The contributor reports the lesion is raised or bumpy · the condition has been present for about one day · no relevant systemic symptoms · the patient considered this a rash · a close-up photograph · the subject is female · reported lesion symptoms include enlargement, pain, burning, bothersome appearance and itching · the lesion involves the leg, arm and back of the hand — 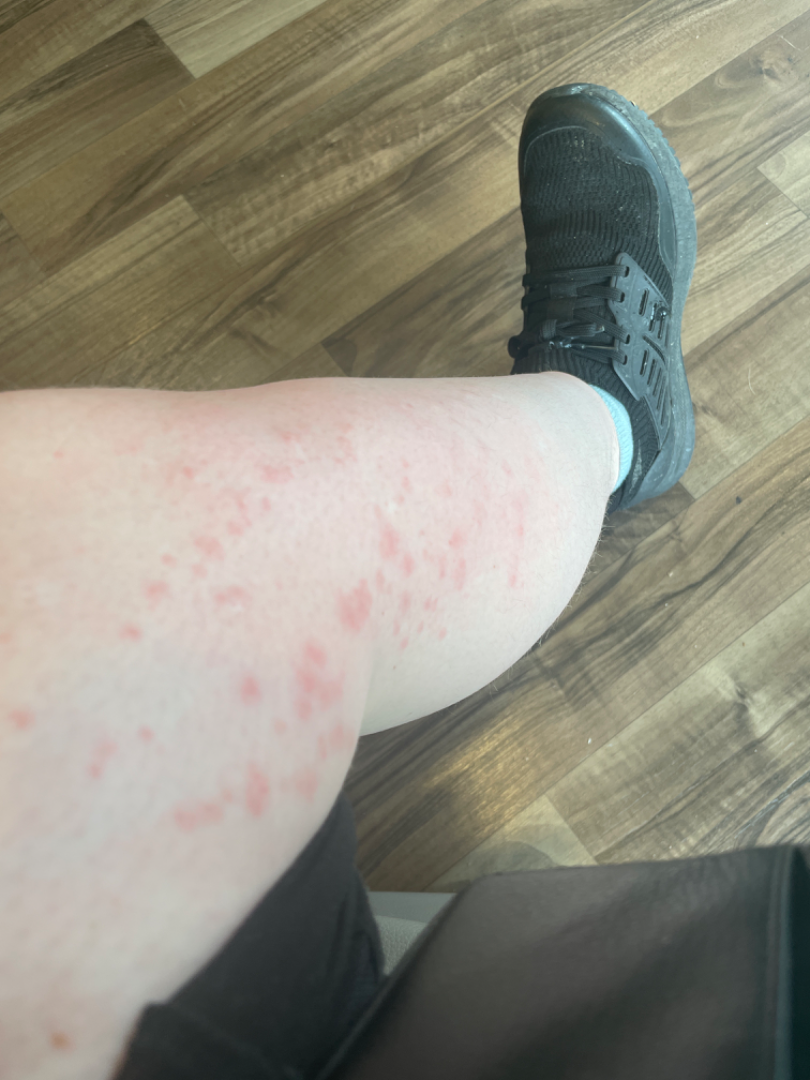The case was indeterminate on photographic review.